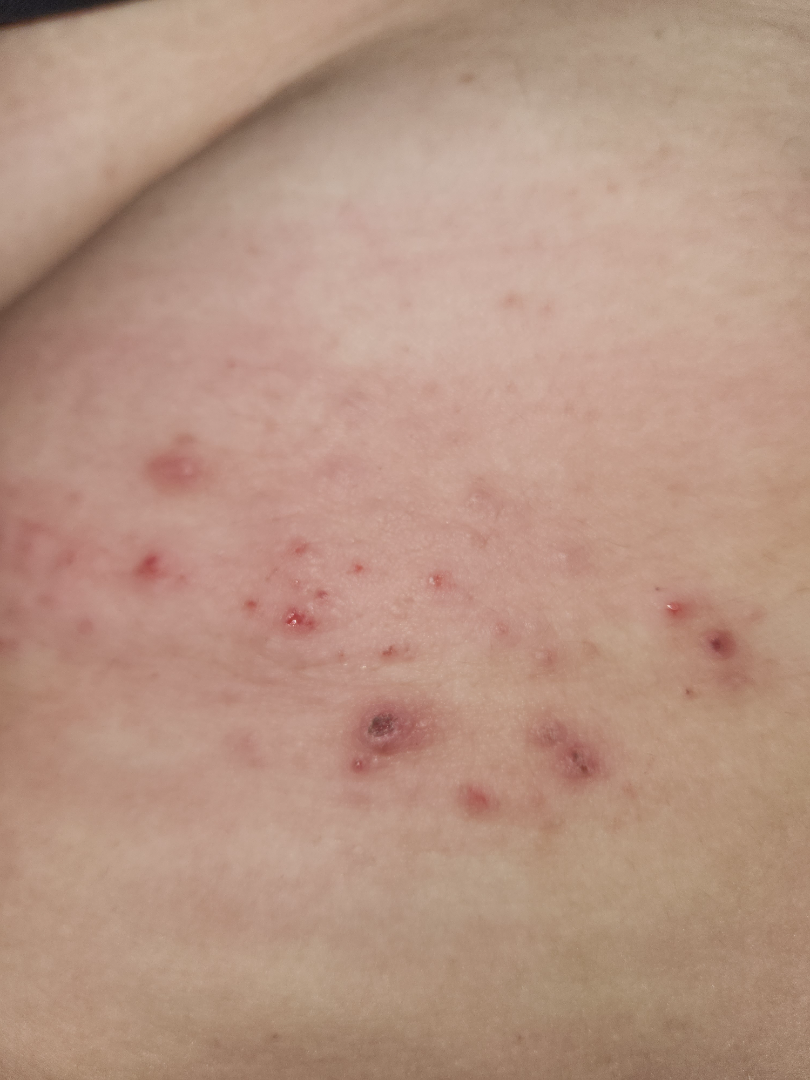shot type: at an angle | skin tone: FST II; human graders estimated MST 2–3 | dermatologist impression: favoring Allergic Contact Dermatitis; also on the differential is Bullous Pemphigoid; also raised was Insect Bite.